An image taken at an angle · the lesion involves the leg · texture is reported as rough or flaky · the patient notes the condition has been present for more than one year · reported lesion symptoms include itching, enlargement, burning, darkening, pain and bothersome appearance · the subject is female · the patient considered this a rash: 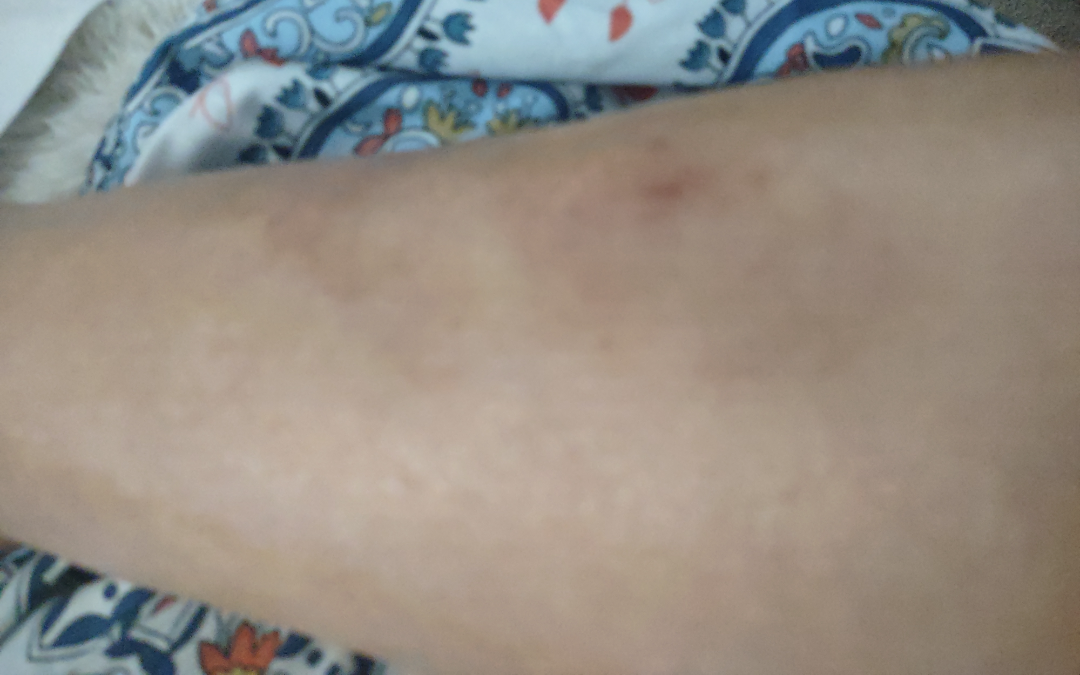<summary>
<differential>
  <leading>Acute and chronic dermatitis</leading>
  <considered>Morphea/Scleroderma, Stasis Dermatitis, Necrobiosis lipoidica</considered>
</differential>
</summary>